The photograph is a close-up of the affected area. The arm is involved:
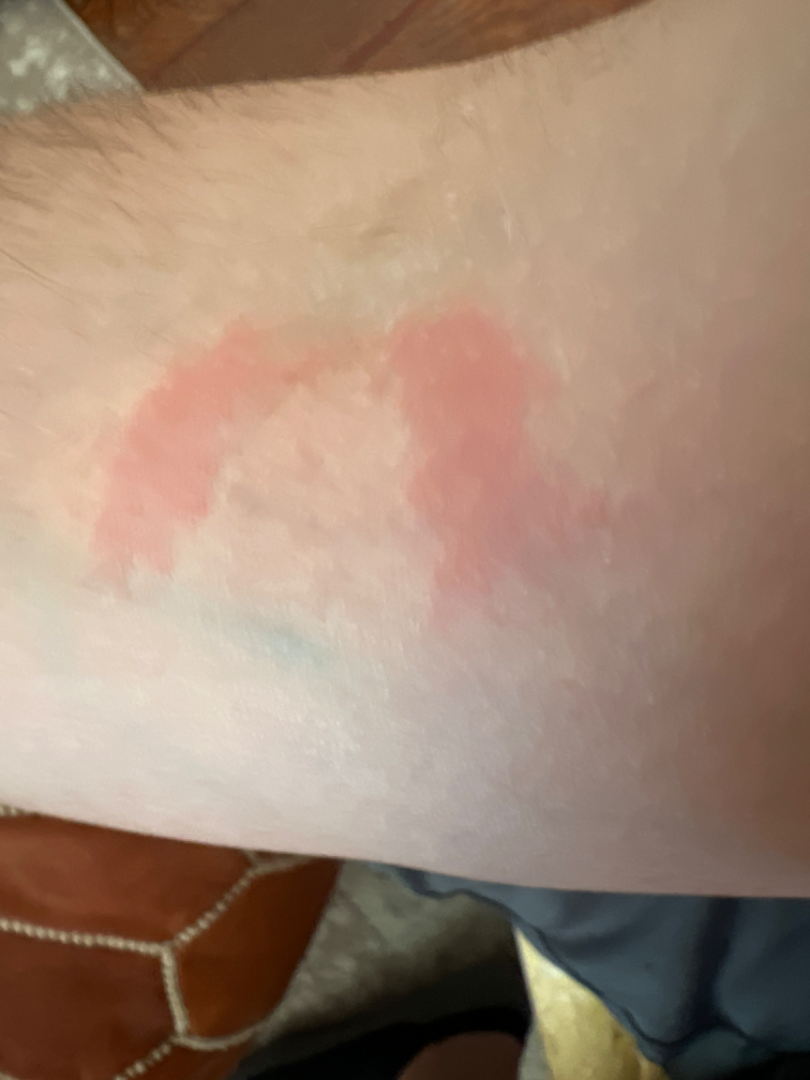* assessment · indeterminate from the photograph